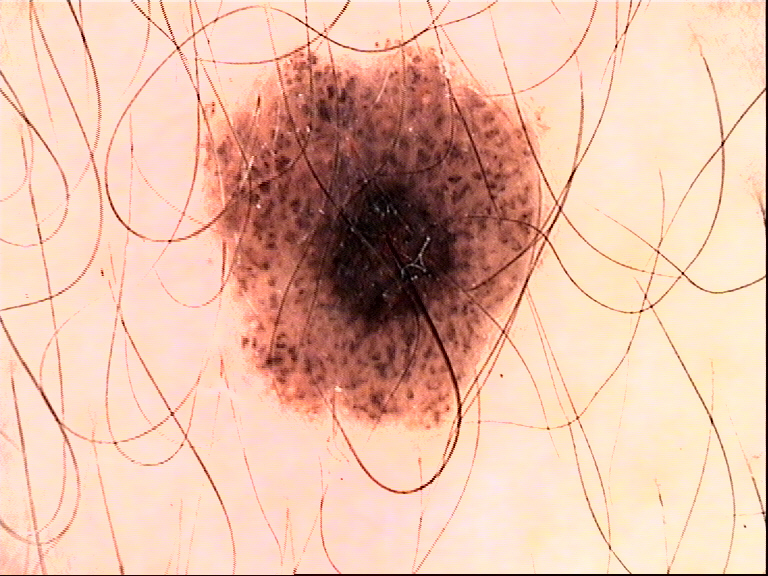Case:
– imaging — dermoscopy
– diagnosis — compound nevus (expert consensus)